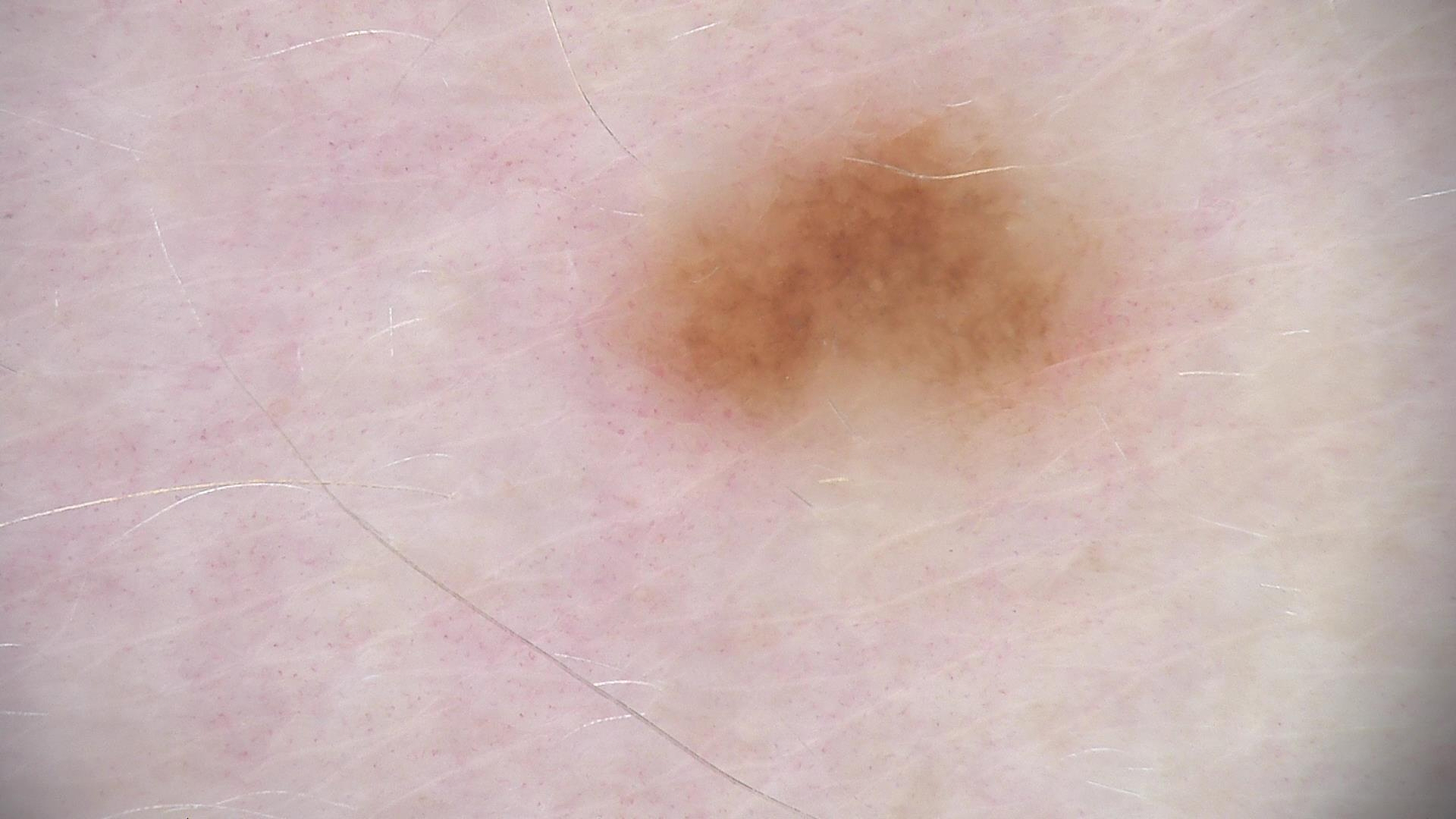• imaging: dermoscopy
• diagnosis: dysplastic junctional nevus (expert consensus)